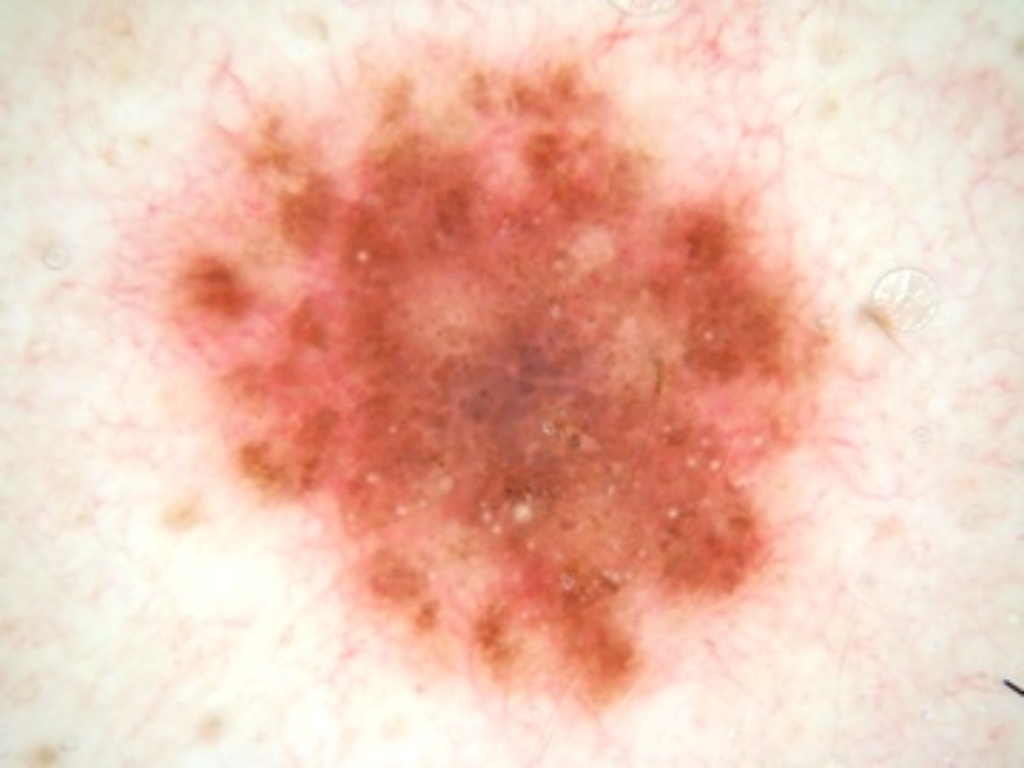| key | value |
|---|---|
| modality | dermoscopic image |
| subject | male, in their mid-30s |
| dermoscopic features | globules, milia-like cysts, and negative network |
| location | <box>105, 24, 866, 738</box> |
| diagnostic label | a melanocytic nevus |